A dermatoscopic image of a skin lesion. Recorded as Fitzpatrick I. A female patient about 80 years old — 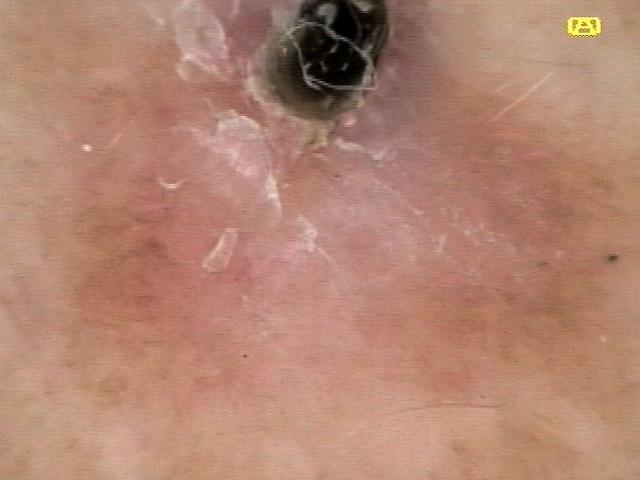pathology: Basal cell carcinoma (biopsy-proven).